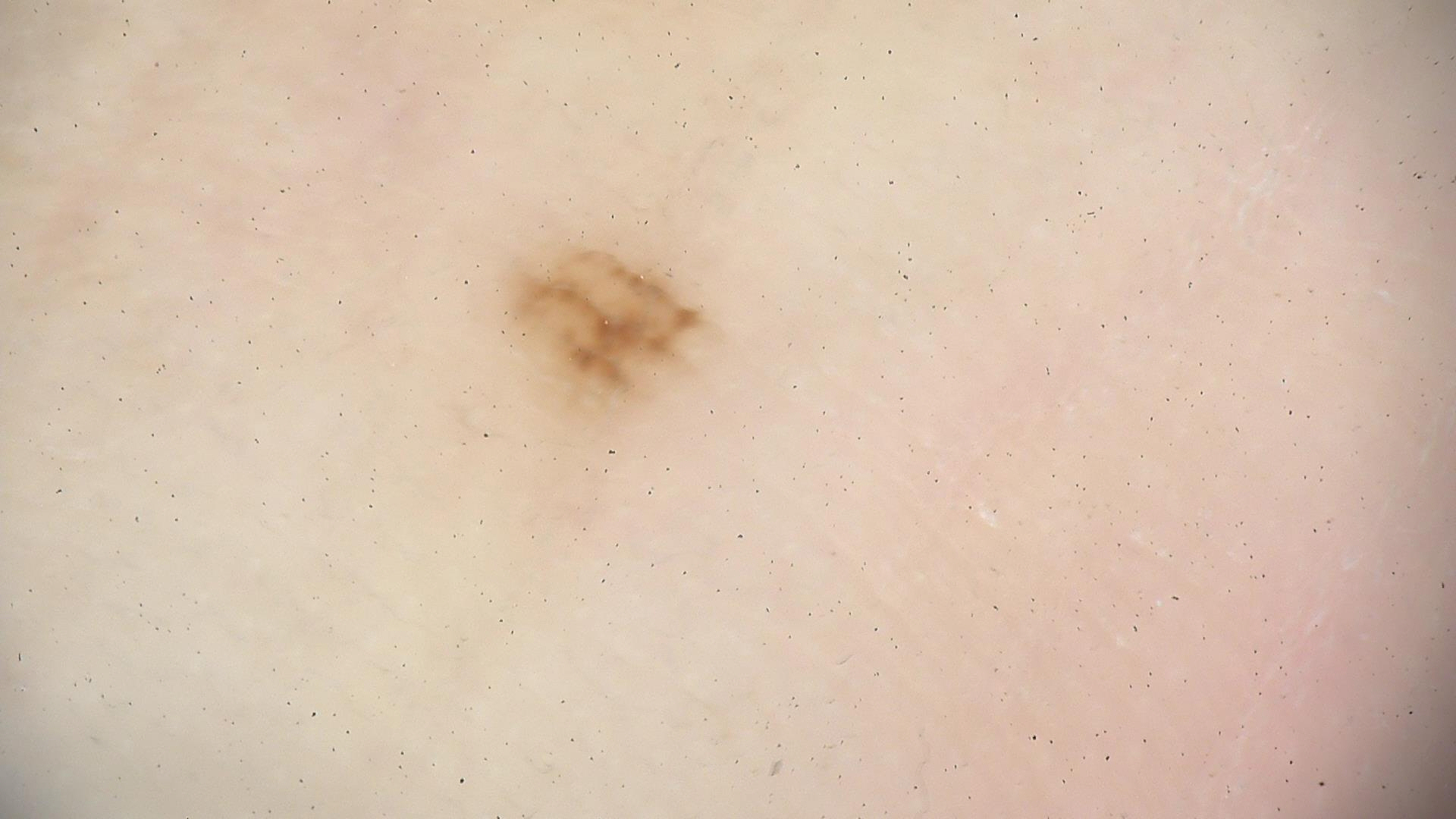A dermoscopy image of a single skin lesion.
The diagnostic label was an acral dysplastic junctional nevus.